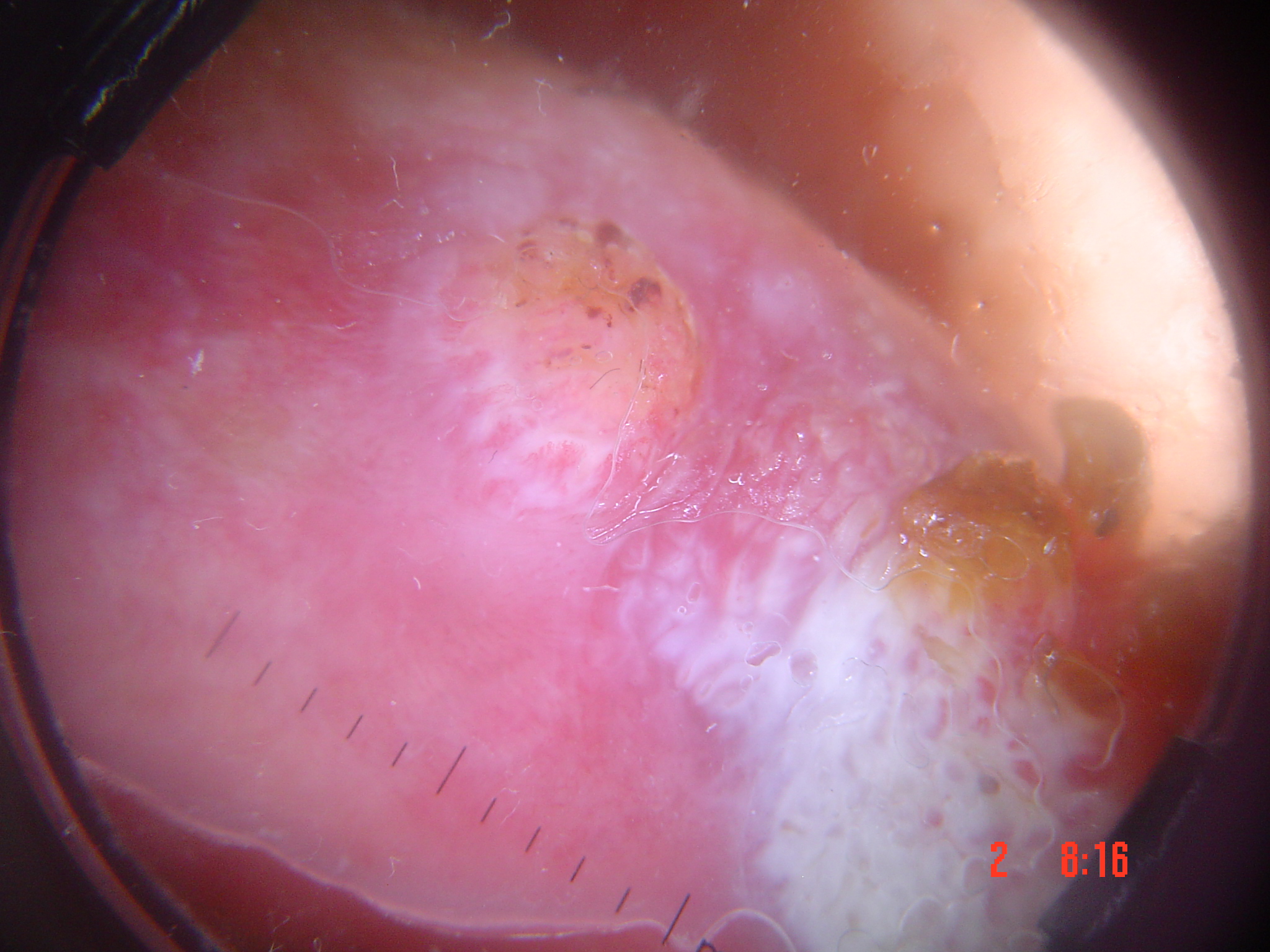Diagnosis: Histopathologically confirmed as a keratinocytic lesion — a squamous cell carcinoma.